The contributor notes itching, the patient described the issue as a rash, the lesion involves the arm, the lesion is described as raised or bumpy, the photograph is a close-up of the affected area.
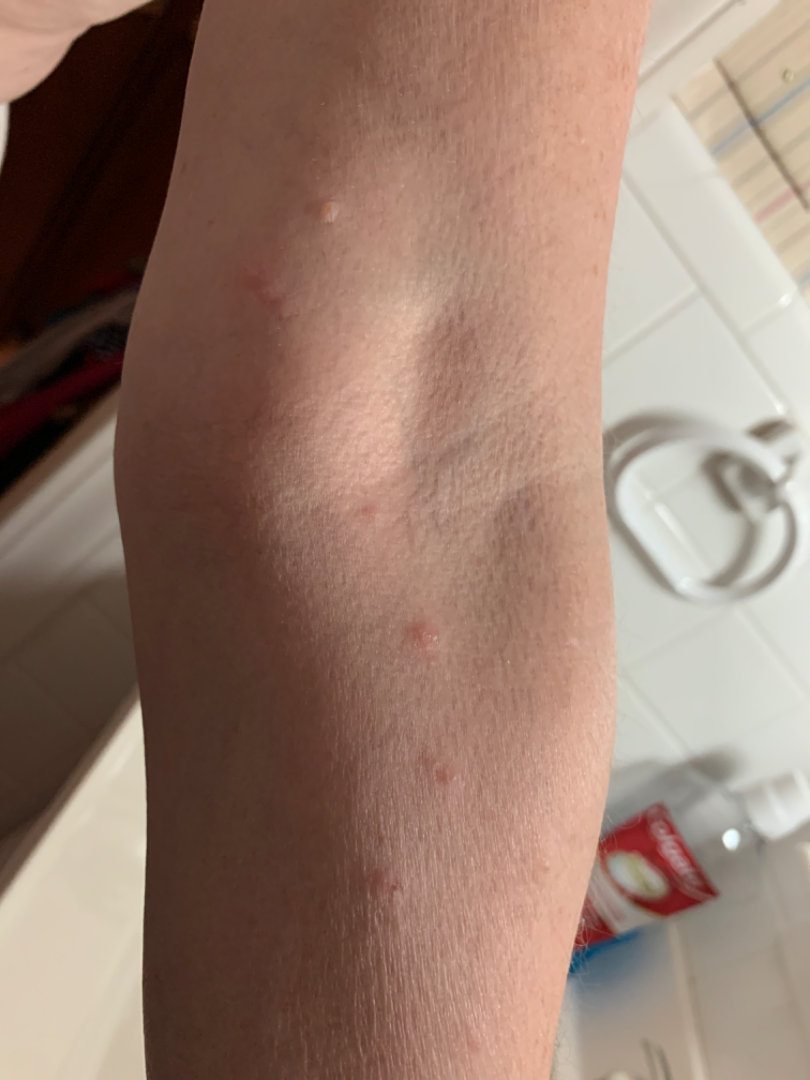On photographic review: Insect Bite (most likely); Herpes Zoster (considered); Allergic Contact Dermatitis (considered).